The lesion involves the arm, the condition has been present for about one day, skin tone: Fitzpatrick skin type IV, close-up view — 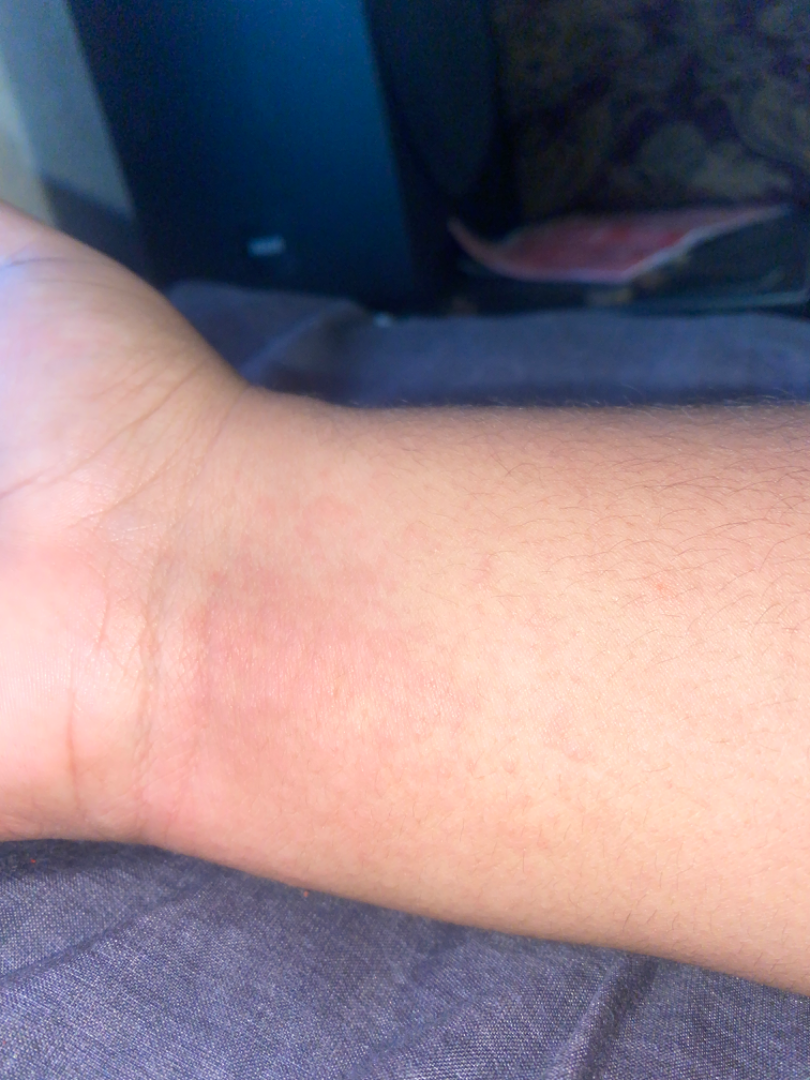Q: What was the assessment?
A: indeterminate from the photograph